Fitzpatrick V; lay reviewers estimated 3 on the Monk skin tone scale. The photograph is a close-up of the affected area.
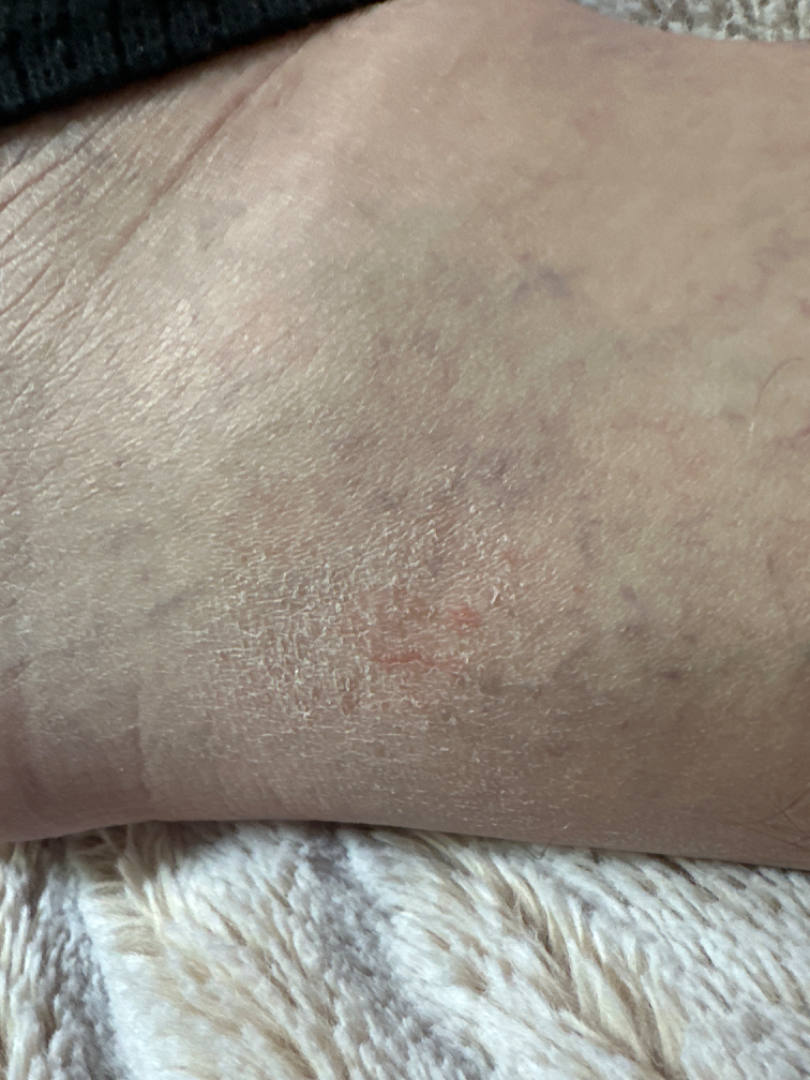differential: the impression was split between Eczema and Stasis Dermatitis